A dermoscopy image of a single skin lesion.
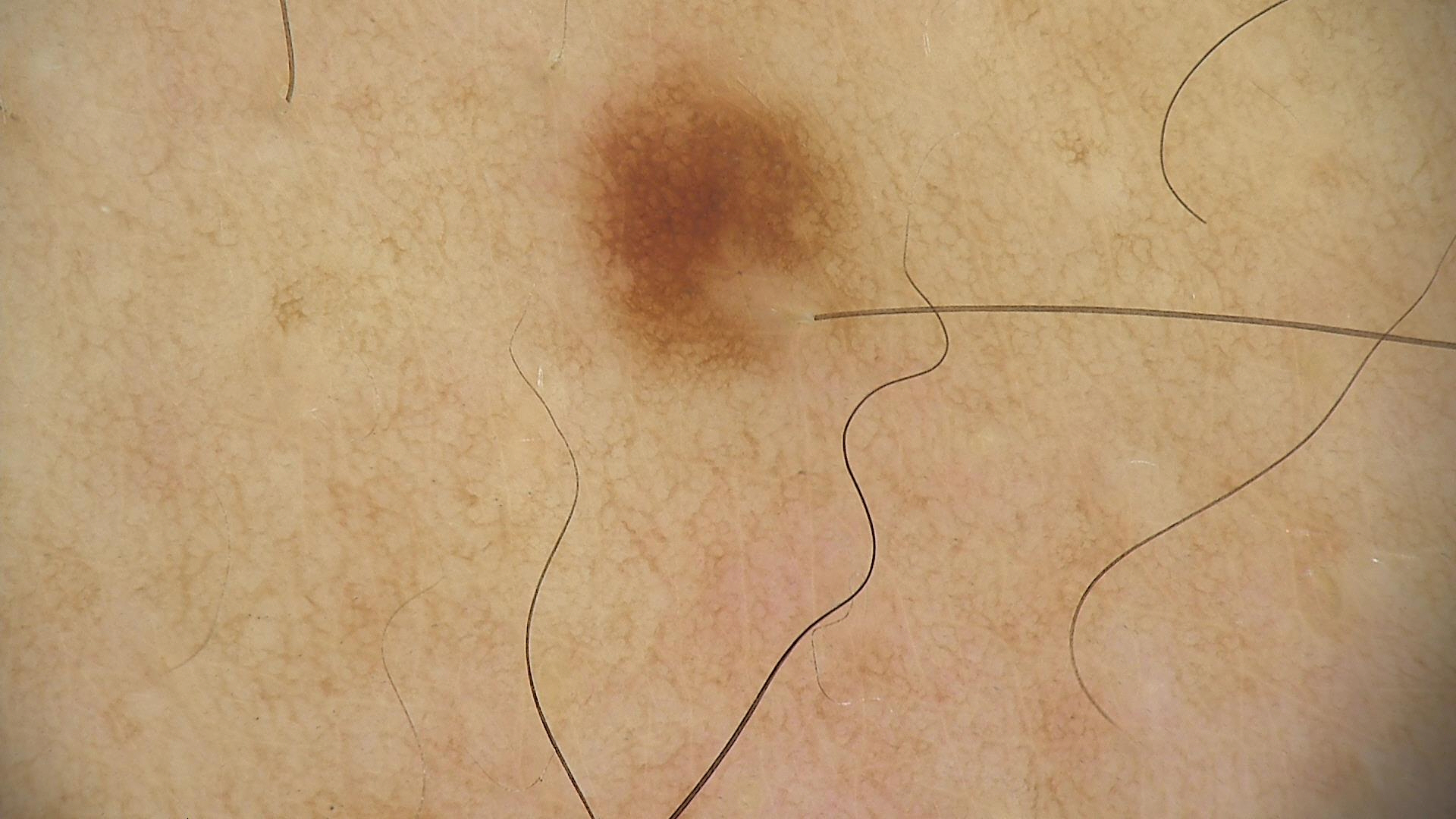diagnostic label: dysplastic junctional nevus (expert consensus).